The patient says their skin reddens with sun exposure. A dermoscopy image of a skin lesion. The patient reports a history of sunbed use, no prior organ transplant, and no personal history of skin cancer. The patient describes having numerous moles. Collected as part of a research study, without a referral diagnosis. A female patient 26 years old.
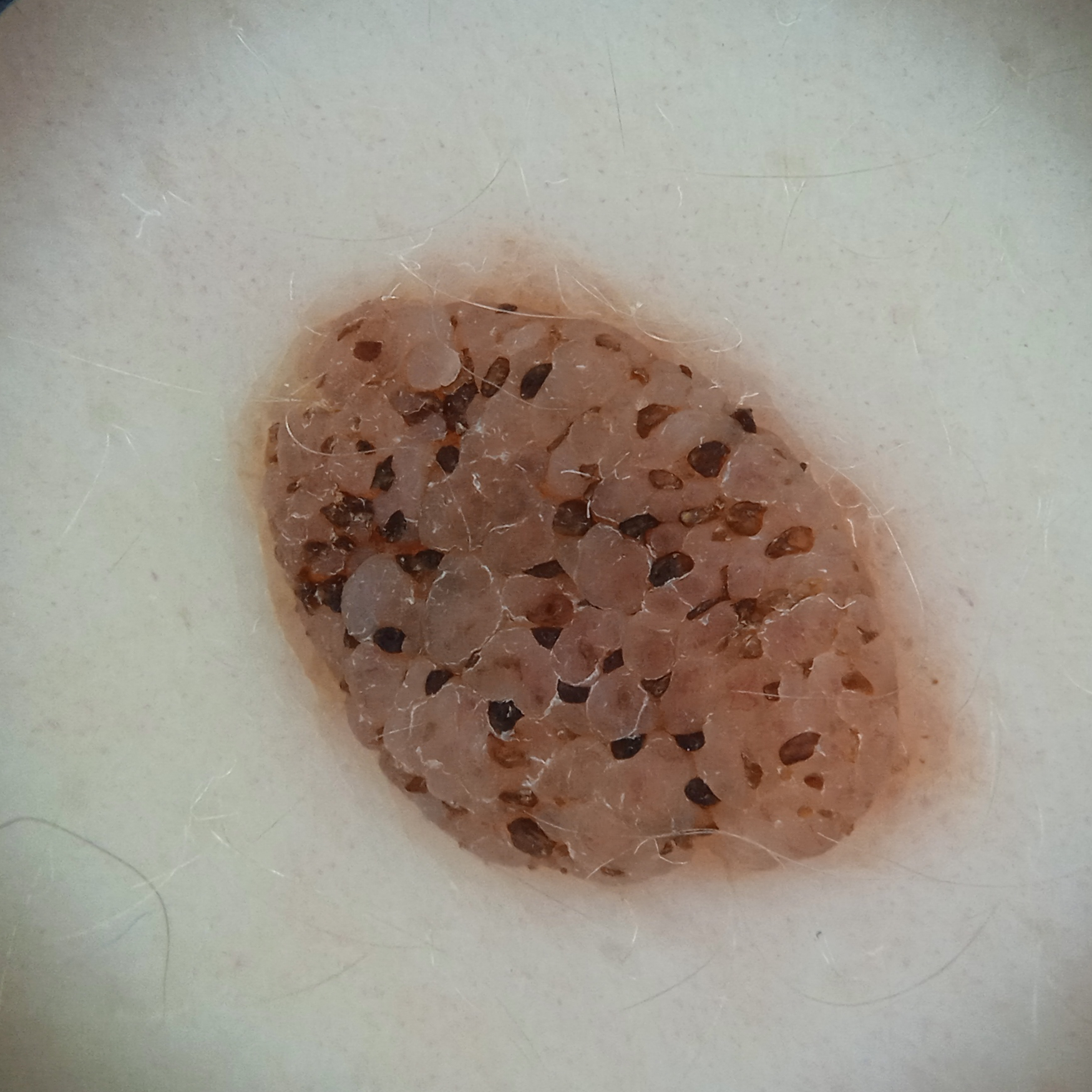Q: What is the anatomic site?
A: the back
Q: How large is the lesion?
A: 8.4 mm
Q: What was the diagnosis?
A: seborrheic keratosis (dermatologist consensus)